Dermoscopy of a skin lesion:
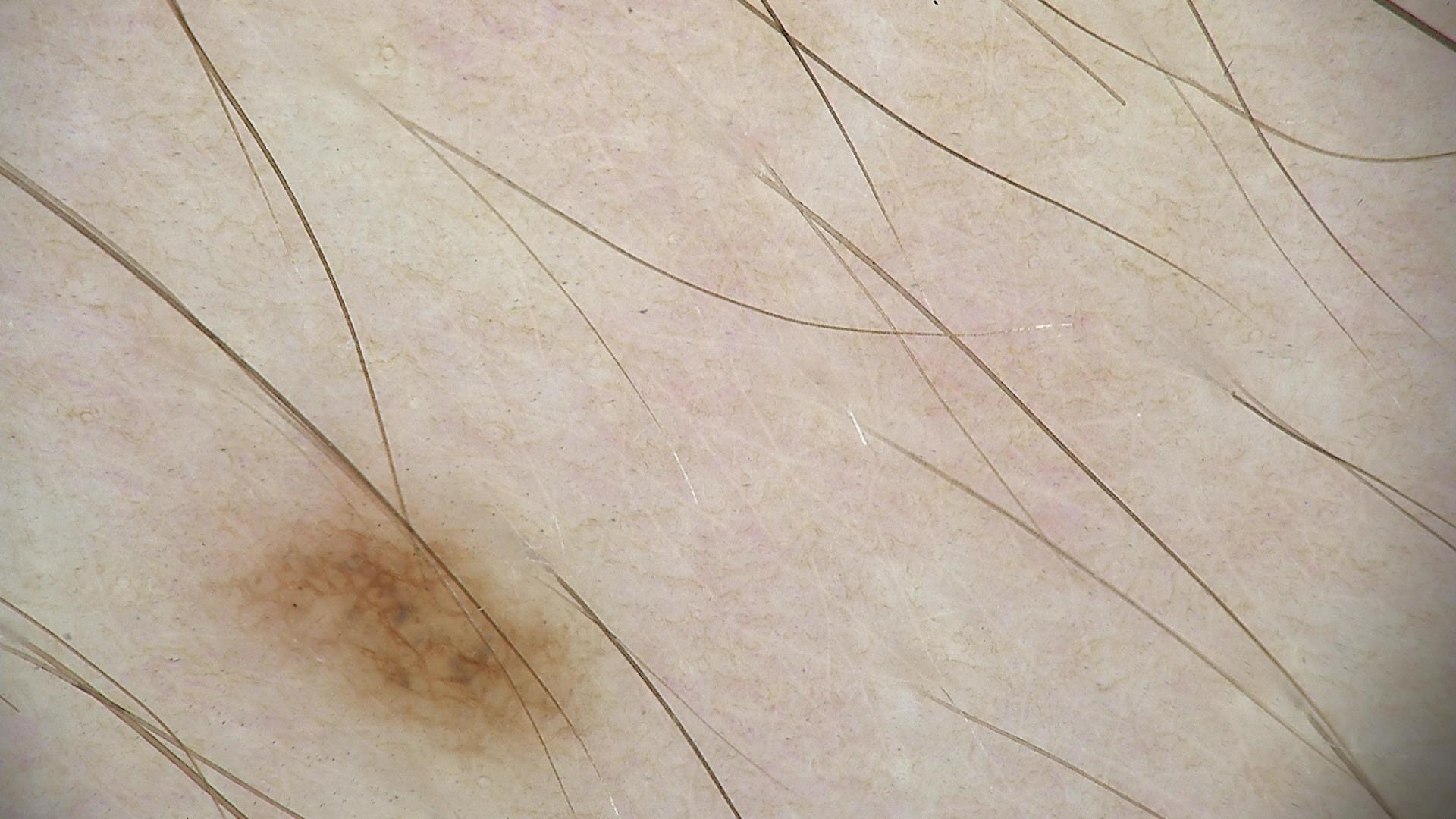The diagnostic label was a dysplastic junctional nevus.